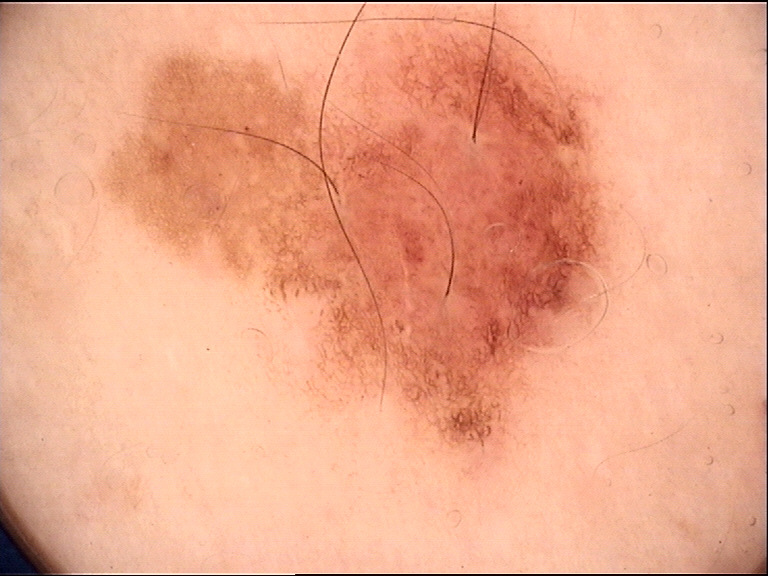class — dysplastic junctional nevus (expert consensus).